The photograph was taken at an angle. The lesion is described as raised or bumpy. No relevant systemic symptoms. The lesion involves the leg: 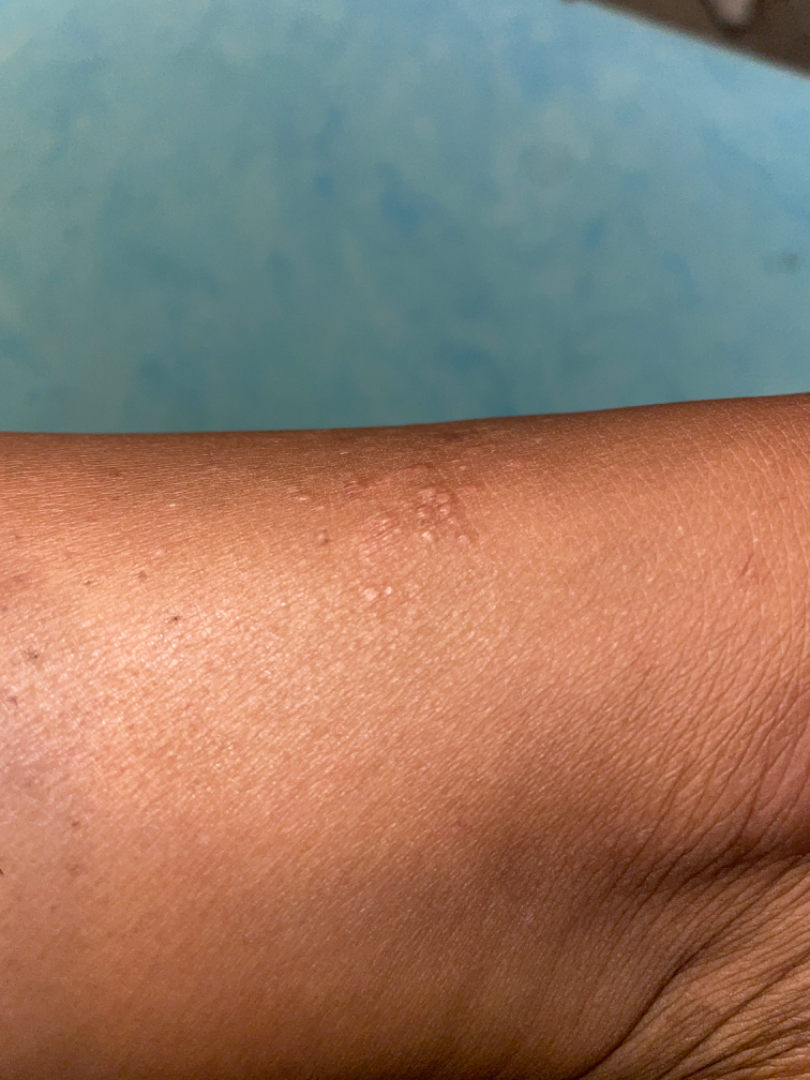differential diagnosis: Eczema (34%); Lichen planus/lichenoid eruption (29%); Lichen nitidus (15%); Allergic Contact Dermatitis (15%); Lichen spinulosus (8%)